The patient reports no prior organ transplant · the patient says their skin reddens painfully with sun exposure · collected as part of a research study, without a referral diagnosis · a clinical photograph showing a skin lesion:
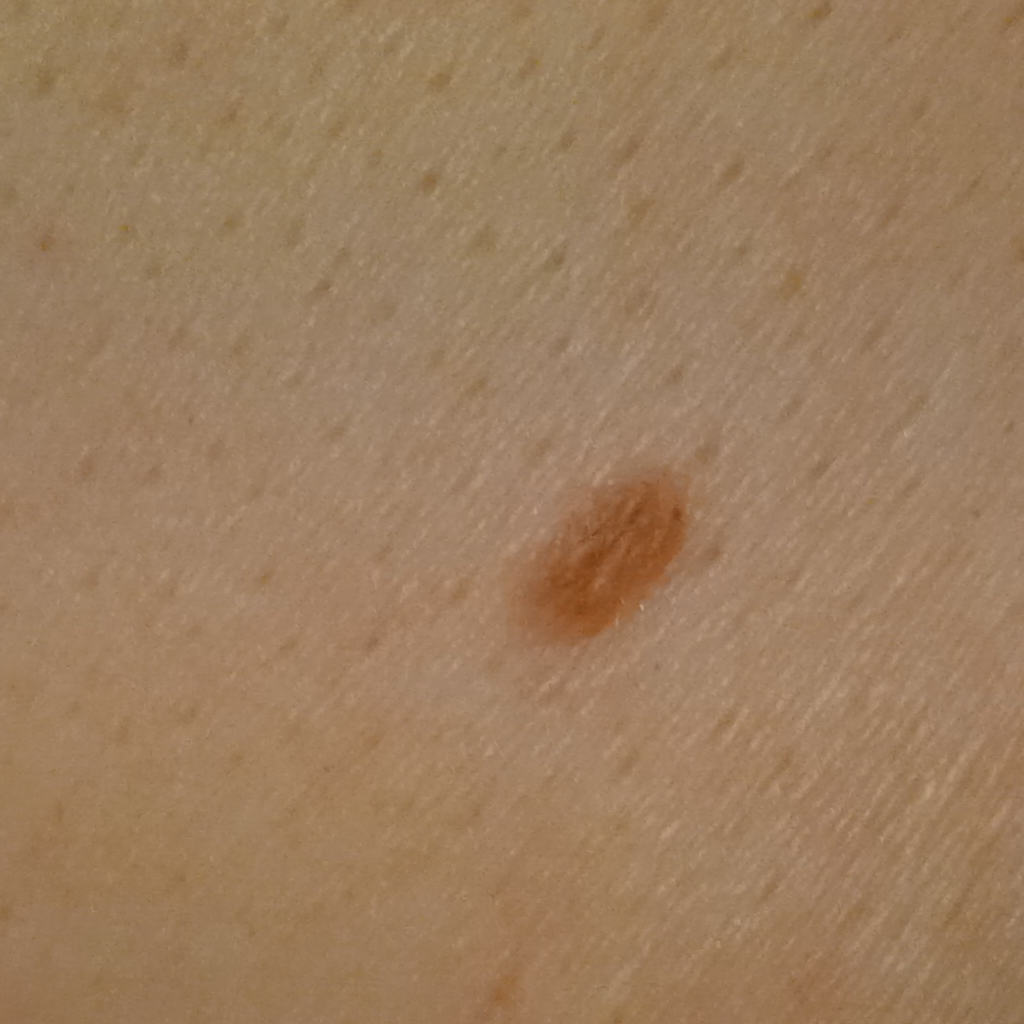size=4.9 mm | diagnosis=melanocytic nevus (dermatologist consensus).